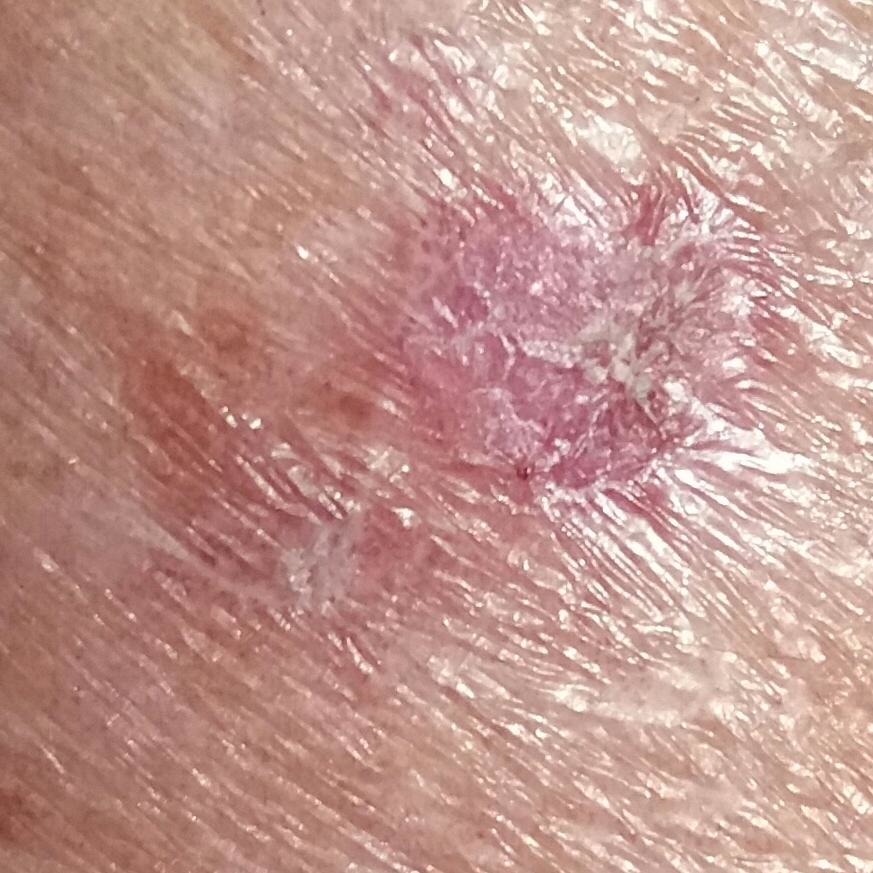  lesion_location: a thigh
  symptoms:
    present:
      - itching
  diagnosis:
    name: squamous cell carcinoma
    code: SCC
    malignancy: malignant
    confirmation: histopathology